The photo was captured at a distance, the contributor reports the condition has been present for less than one week:
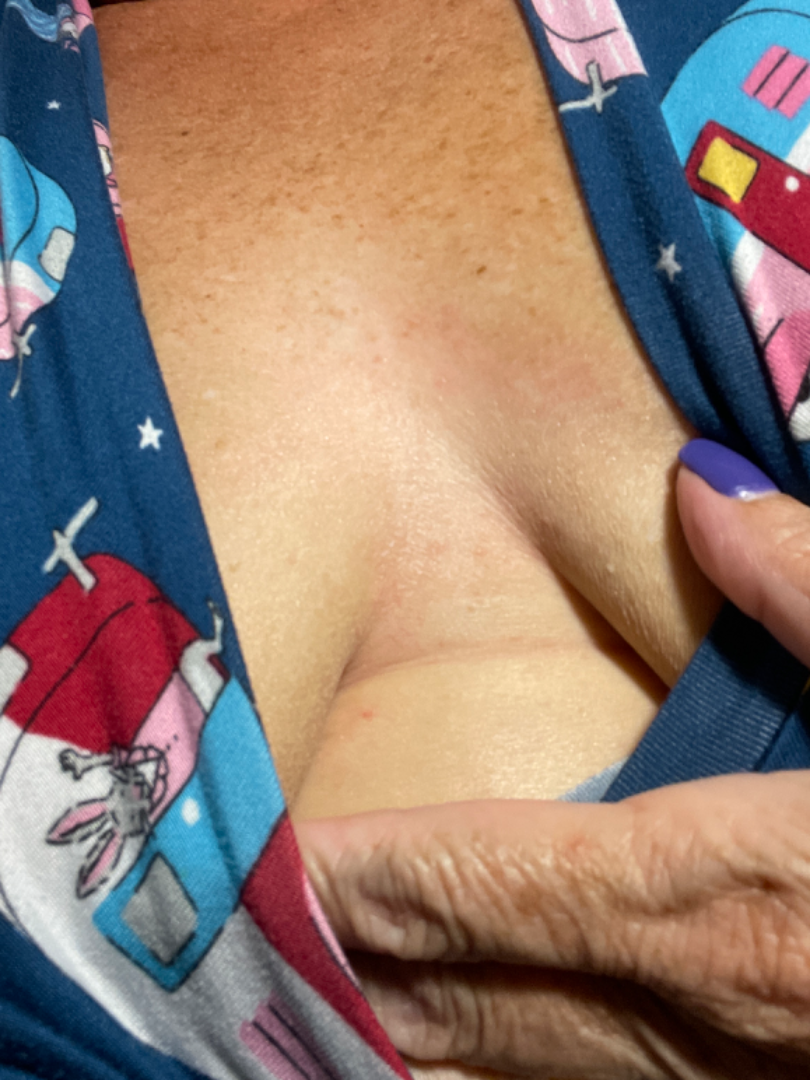{
  "assessment": "not assessable"
}